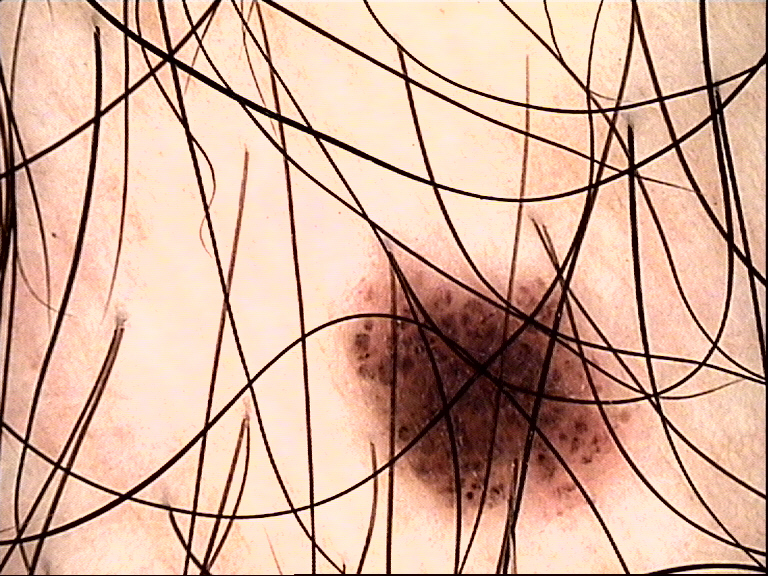image: dermoscopy
diagnosis:
  name: dysplastic compound nevus
  code: cd
  malignancy: benign
  super_class: melanocytic
  confirmation: expert consensus